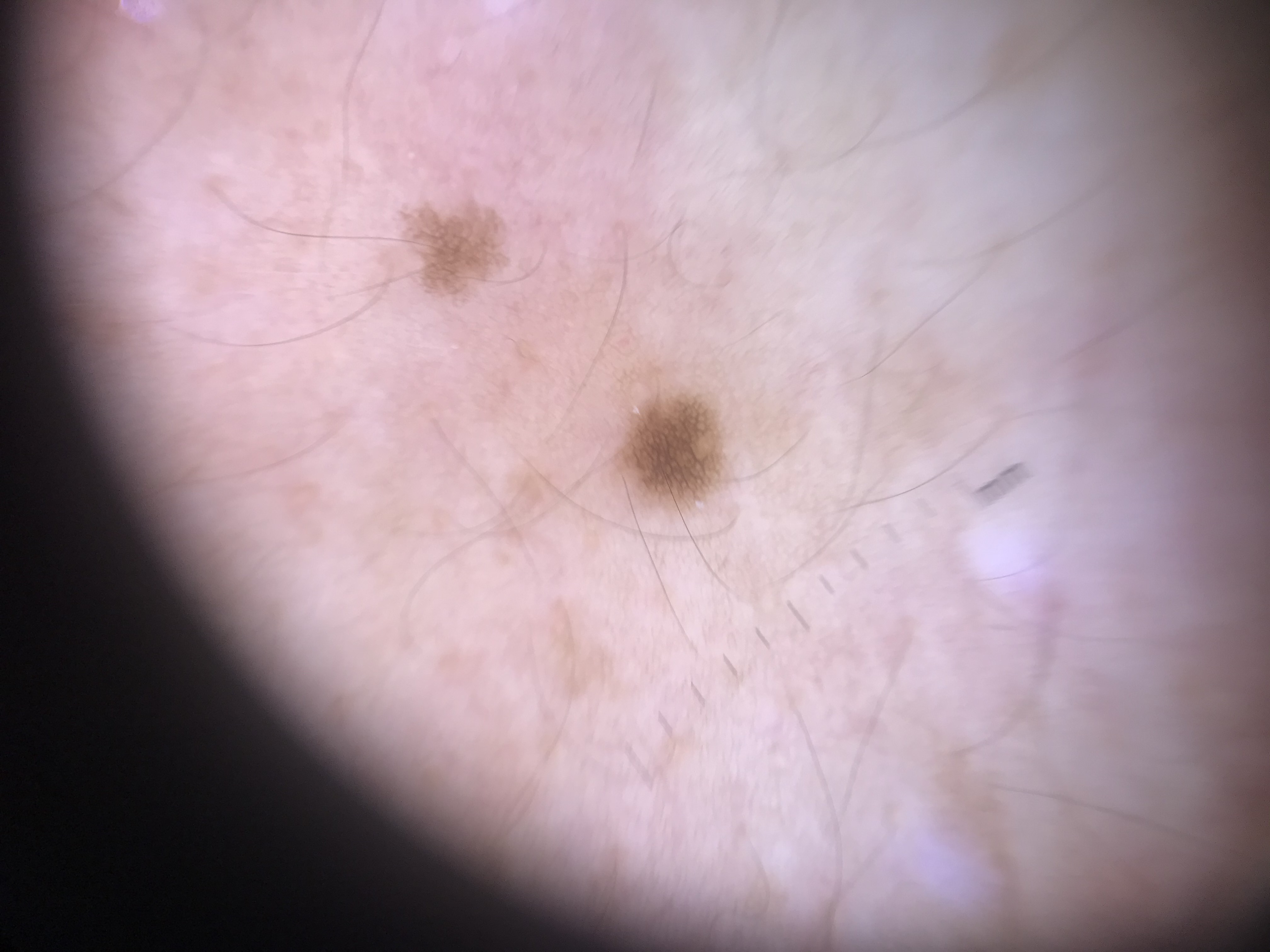label: junctional nevus (expert consensus).